Skin tone: Fitzpatrick skin type II · the subject is male · symptoms reported: bothersome appearance and itching · the patient considered this a rash · texture is reported as raised or bumpy · present for one to four weeks · close-up view · the affected area is the arm:
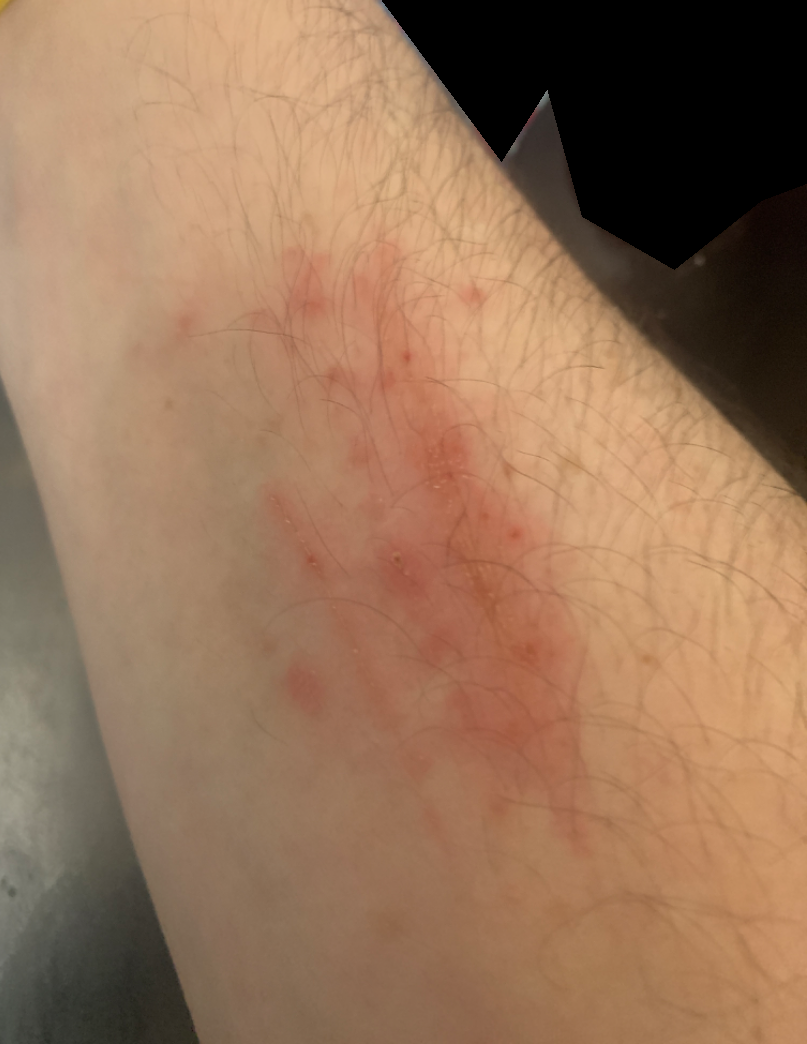Impression: On photographic review: the leading consideration is Superficial wound of body region; also on the differential is Skin and soft tissue atypical mycobacterial infection; possibly SCC/SCCIS.